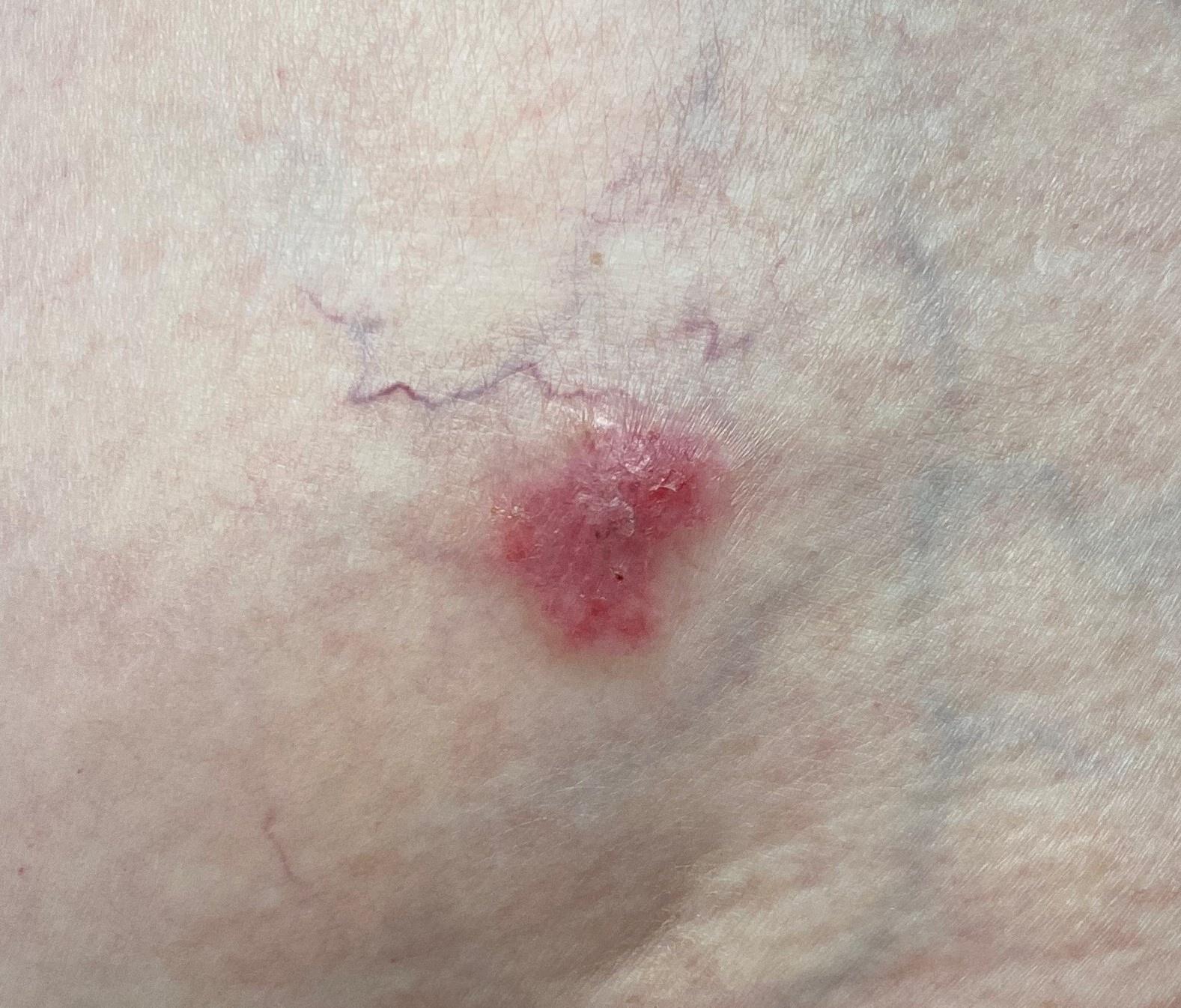diagnostic label: Basal cell carcinoma (biopsy-proven)